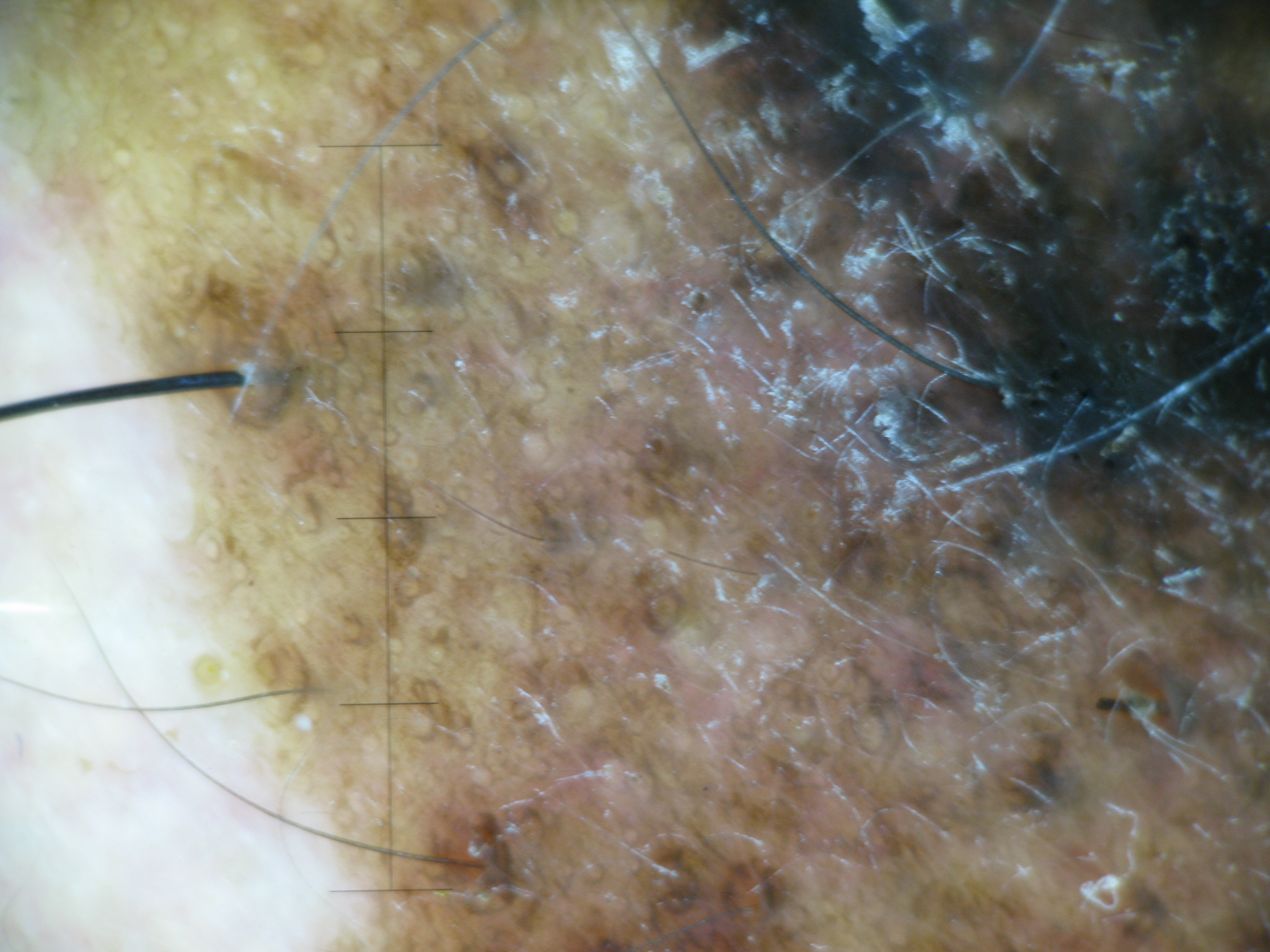A dermoscopic close-up of a skin lesion.
Biopsy-confirmed as a lentigo maligna melanoma.